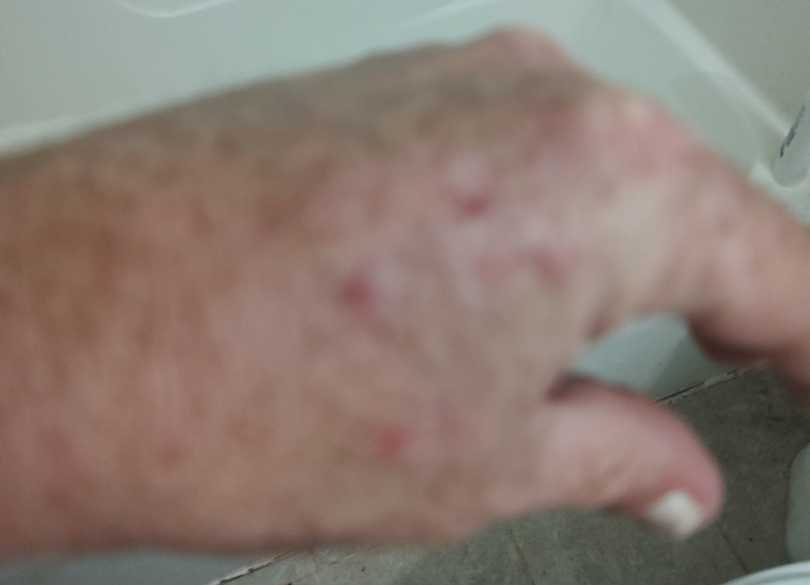The case was indeterminate on photographic review. This is a close-up image.